The lesion involves the arm and leg. The photograph is a close-up of the affected area. Female subject, age 18–29.
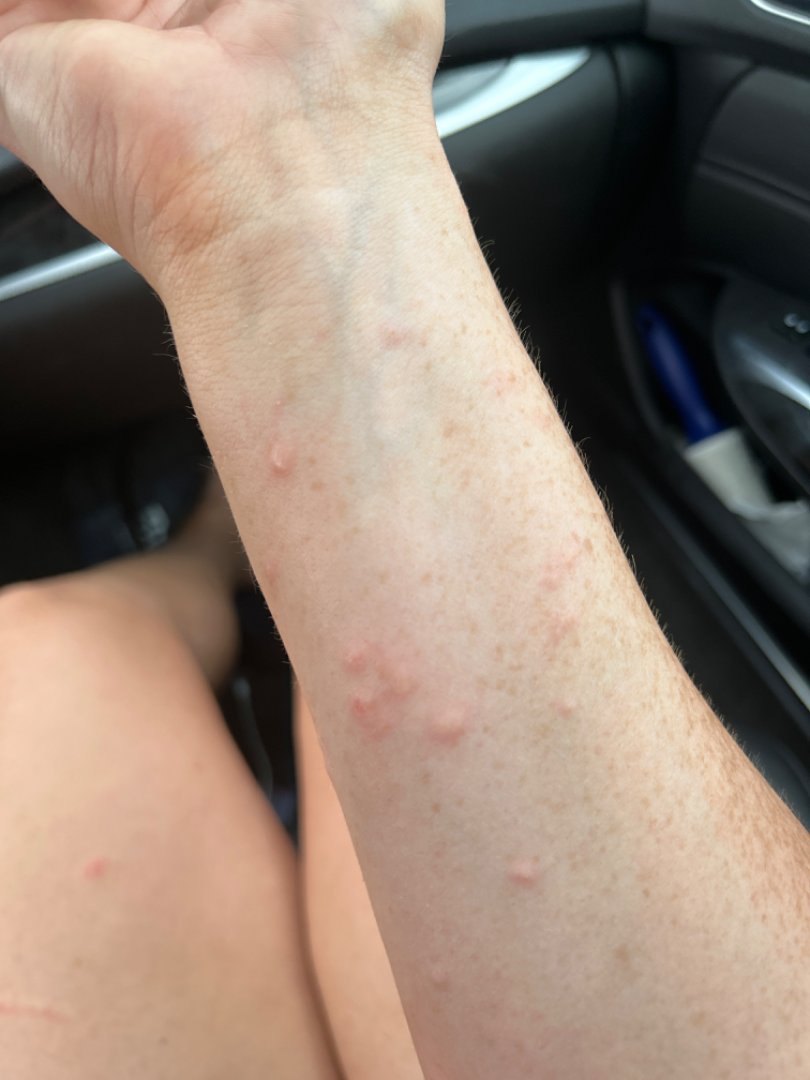history: about one day, self-categorized as: a rash, differential diagnosis: the leading consideration is Insect Bite; an alternative is Urticaria; also raised was Allergic Contact Dermatitis.